Imaged for a research study, with no referral diagnosis recorded · dermoscopy of a skin lesion · a male subject age 89:
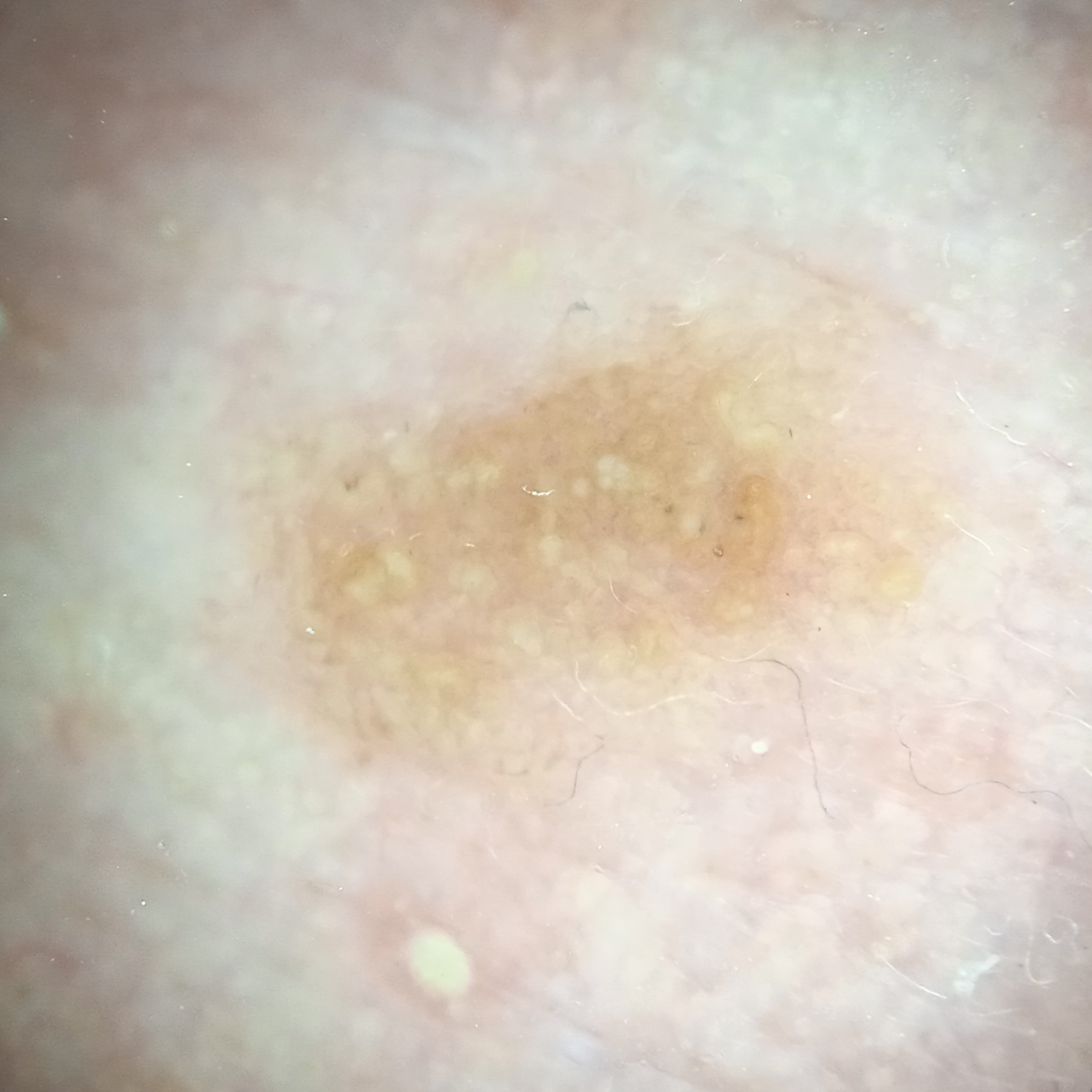The lesion is on the face.
The lesion is about 6.4 mm across.
The consensus diagnosis for this lesion was an actinic keratosis.